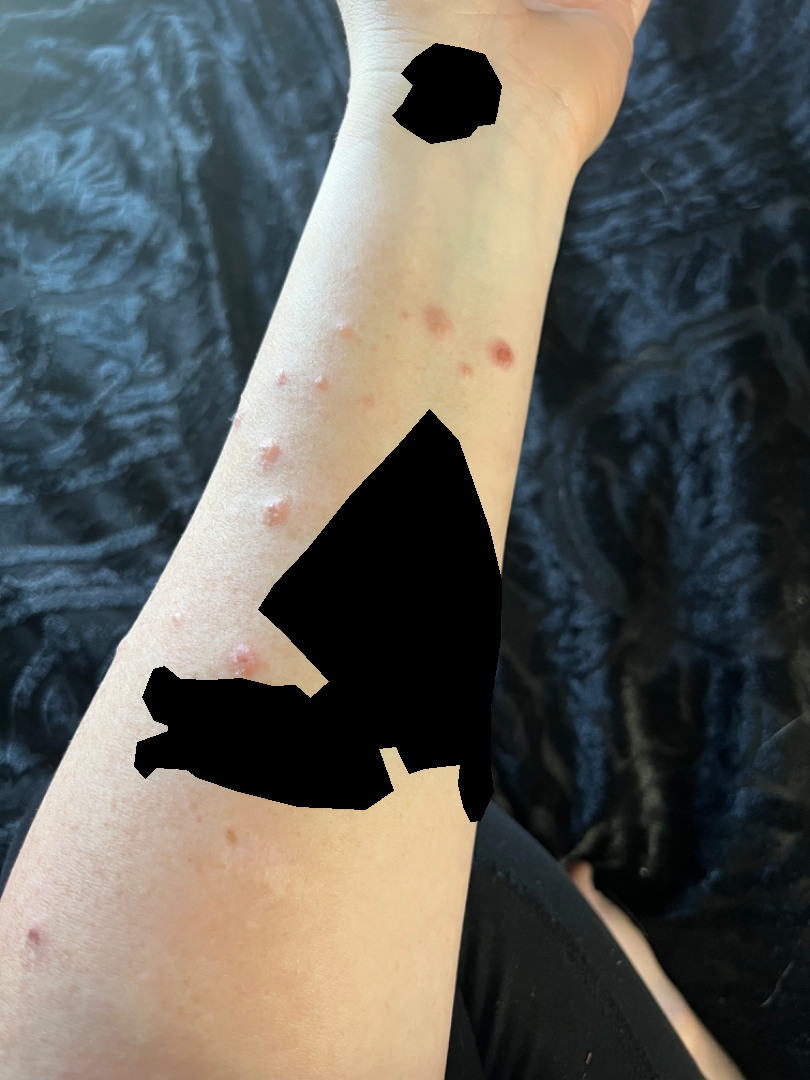Case summary:
* duration: less than one week
* image framing: at a distance
* subject: female, age 18–29
* described texture: fluid-filled, rough or flaky and raised or bumpy
* self-categorized as: a rash
* affected area: back of the torso, arm, front of the torso and head or neck
* other reported symptoms: none reported
* assessment: the impression was split between Prurigo nodularis, Lymphomatoid papulosis and Pityriasis lichenoides